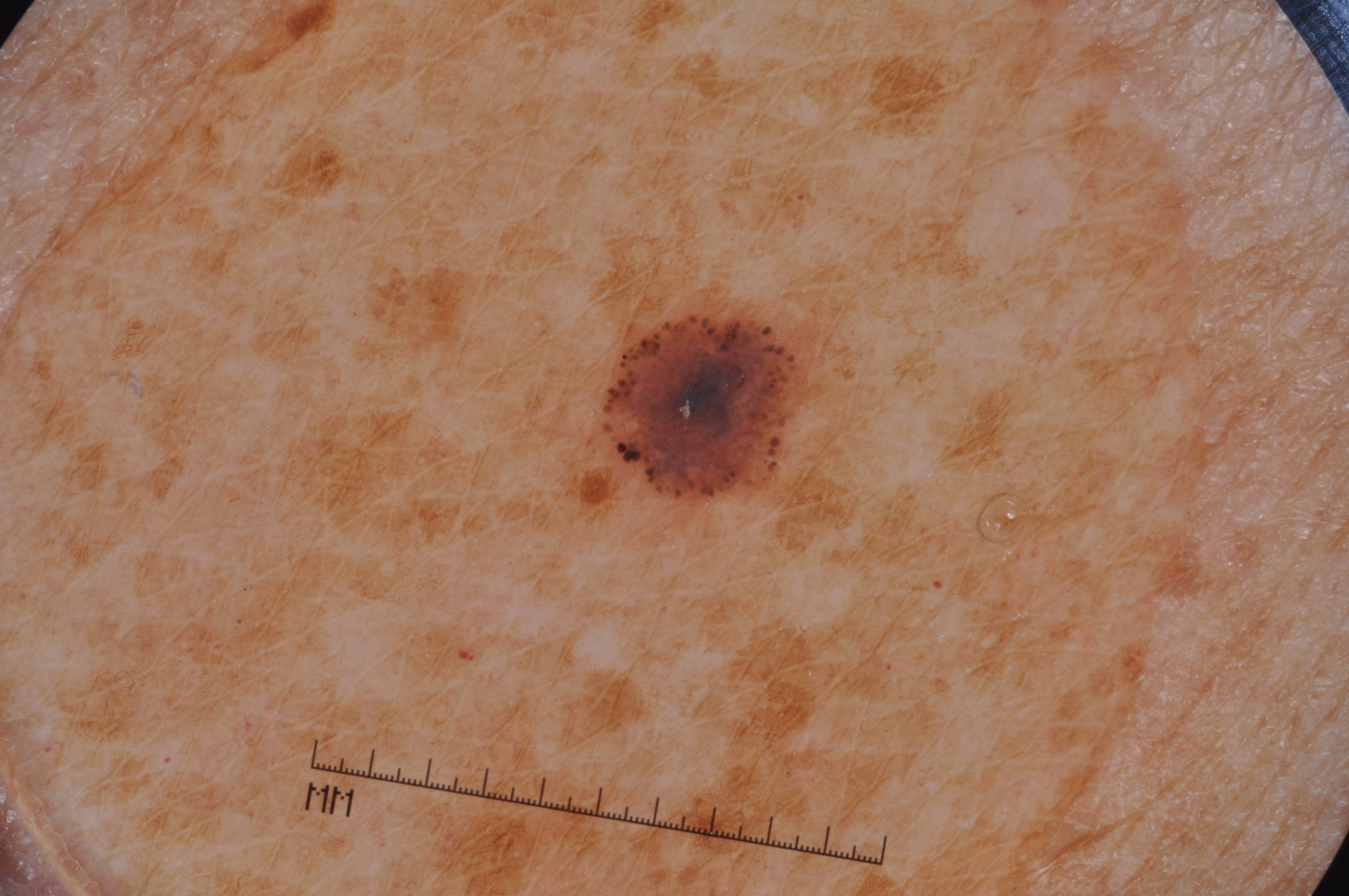A dermoscopy image of a single skin lesion.
Dermoscopic review identifies no pigment network, milia-like cysts, streaks, or negative network.
As (left, top, right, bottom), the lesion spans box(601, 309, 815, 502).
A small lesion within a wider field of skin.
Diagnosed as a melanocytic nevus, a benign skin lesion.